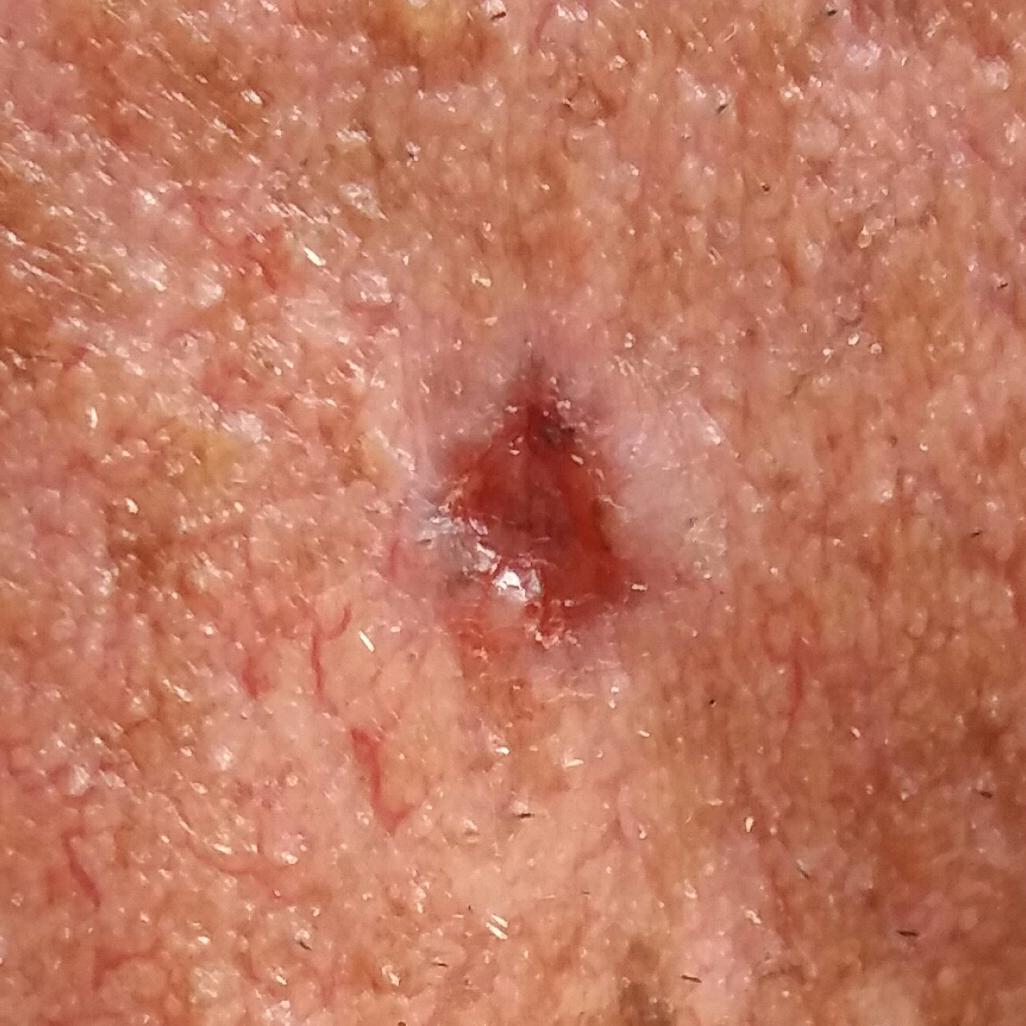{
  "risk_factors": {
    "positive": [
      "prior cancer (patient or family)"
    ]
  },
  "patient": {
    "age": 80,
    "gender": "male"
  },
  "image": "clinical photograph",
  "lesion_location": "the face",
  "lesion_size": {
    "diameter_1_mm": 7.0,
    "diameter_2_mm": 5.0
  },
  "symptoms": {
    "present": [
      "bleeding",
      "elevation",
      "growth",
      "itching"
    ],
    "absent": [
      "pain",
      "change in appearance"
    ]
  },
  "diagnosis": {
    "name": "basal cell carcinoma",
    "code": "BCC",
    "malignancy": "malignant",
    "confirmation": "histopathology"
  }
}